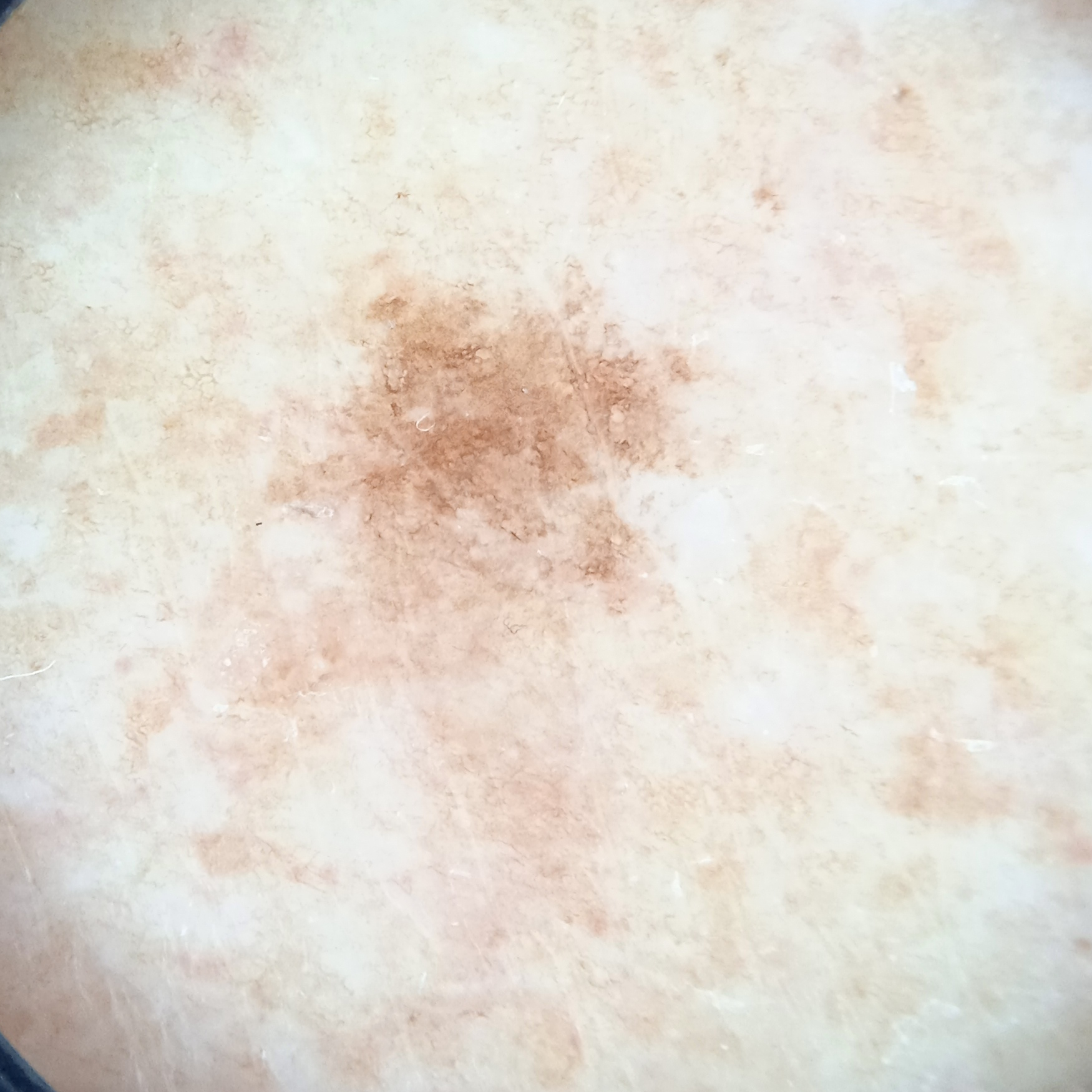patient:
  age: 72
  sex: female
lesion_location: a leg
lesion_size:
  diameter_mm: 6.2
diagnosis:
  name: melanocytic nevus
  malignancy: benign
  unanimous: false
  certainty: moderate